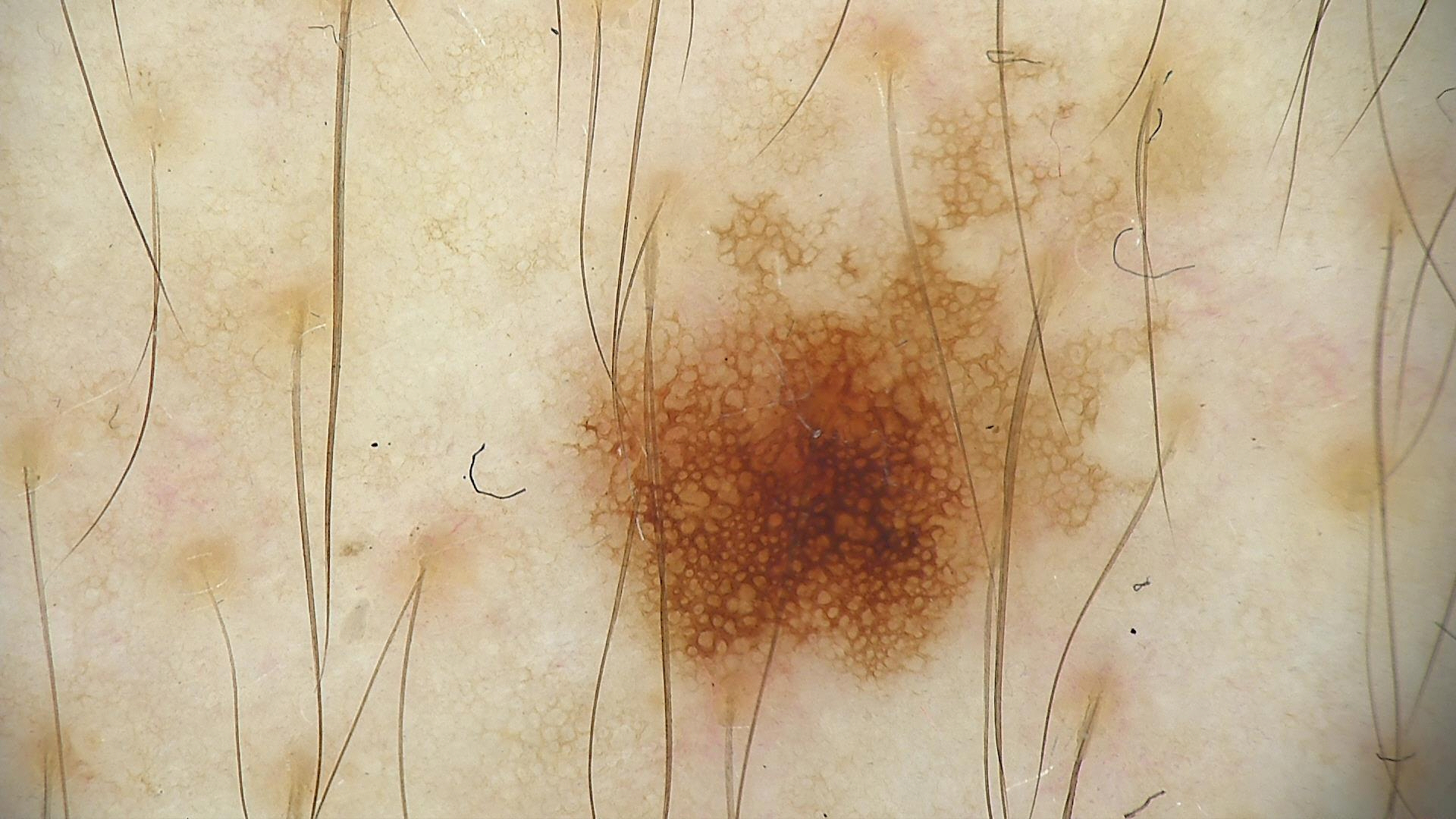Case: A skin lesion imaged with a dermatoscope. Impression: The diagnostic label was a dysplastic junctional nevus.